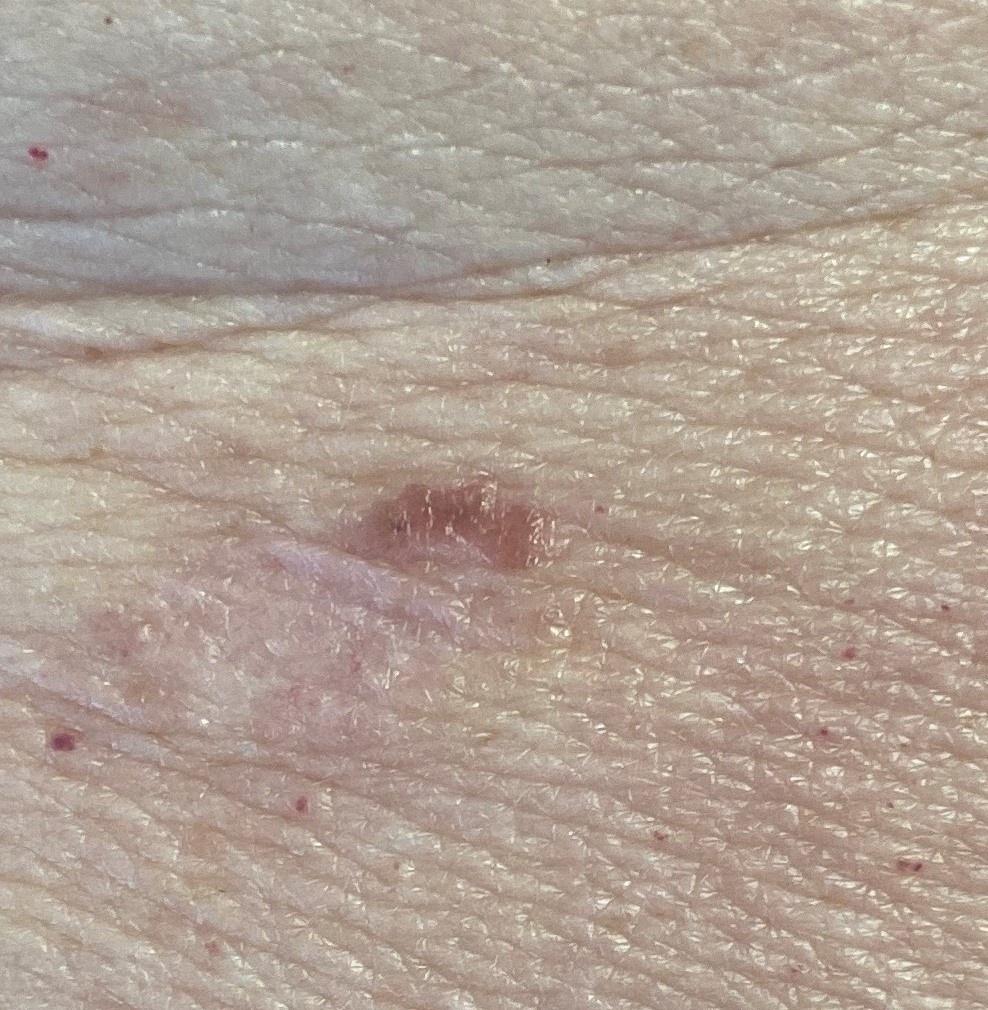Case summary:
A wide-field clinical photograph of a skin lesion. A female subject aged approximately 70. The lesion involves the anterior trunk.
Pathology:
On biopsy, the diagnosis was a basal cell carcinoma.